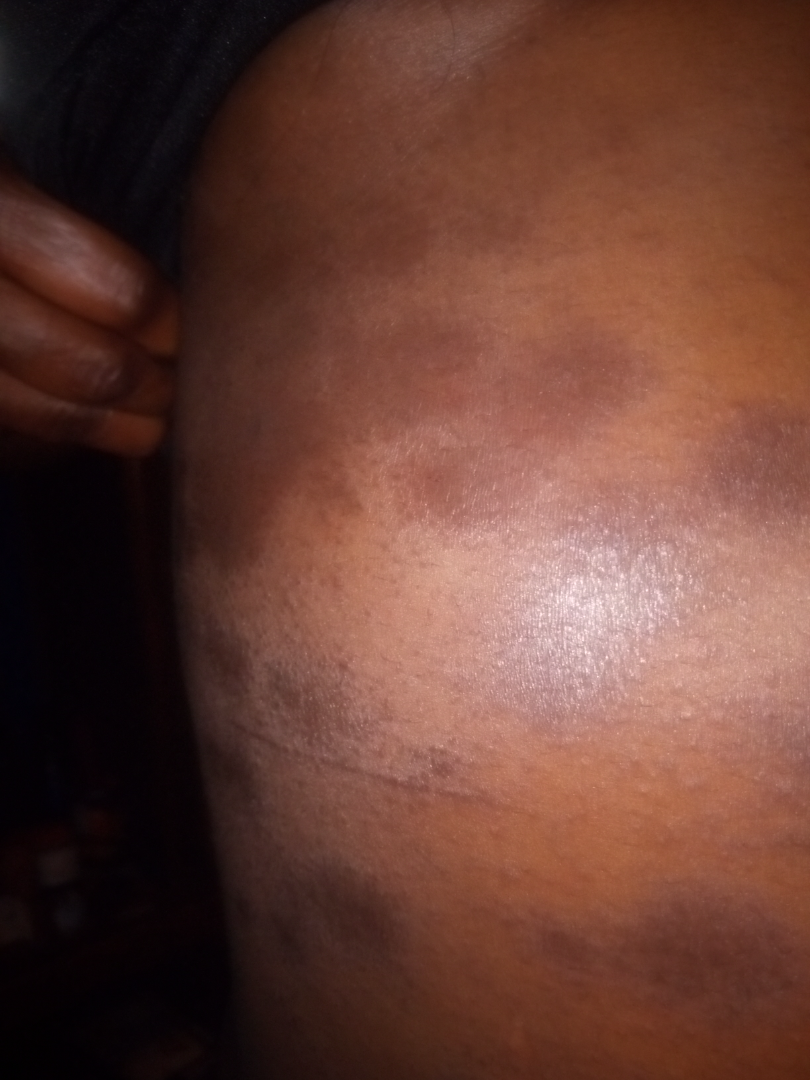No differential diagnosis could be assigned on photographic review.